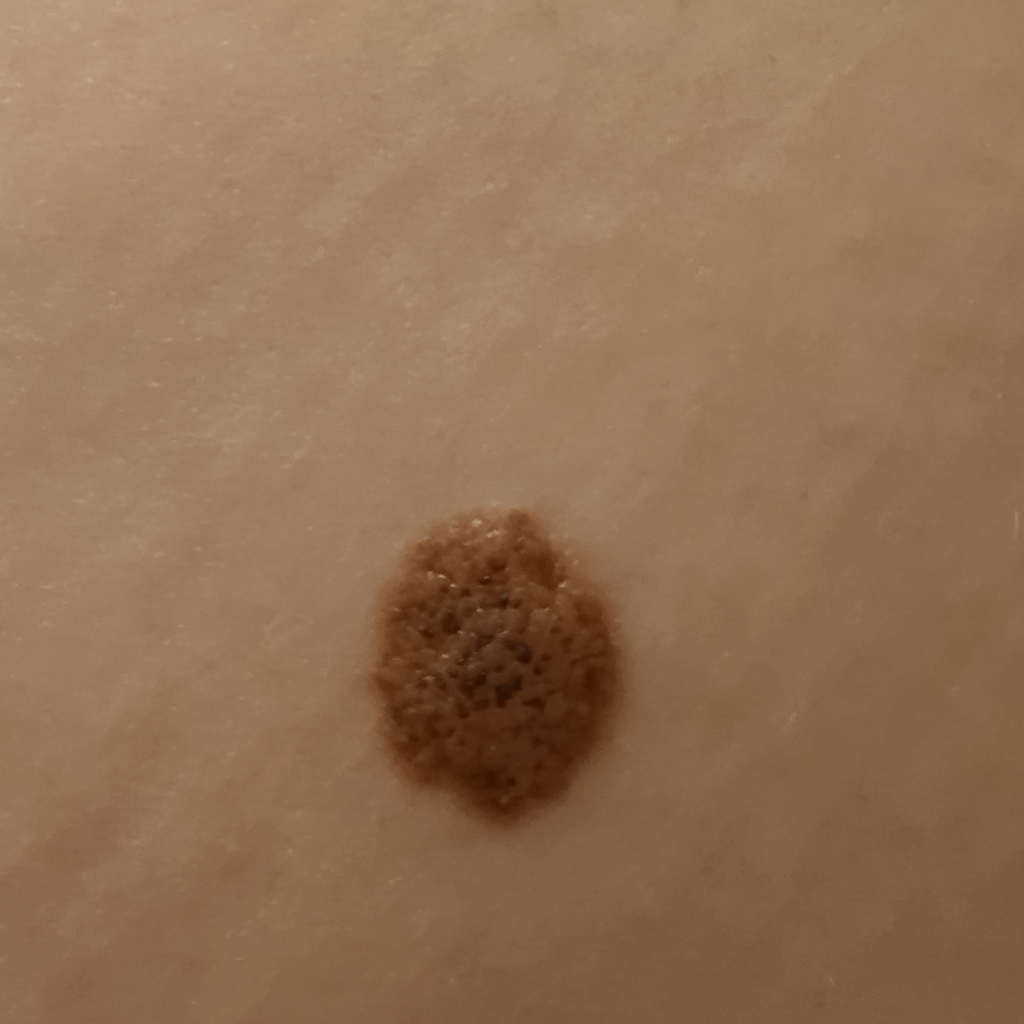subject: female, 26 years old
risk factors: a history of sunbed use
image: clinical photo
size: 12.1 mm
assessment: melanocytic nevus (dermatologist consensus)